A clinical photograph showing a skin lesion · the chart records prior malignancy (patient or family) · a female patient in their late 70s · the patient is Fitzpatrick phototype II — 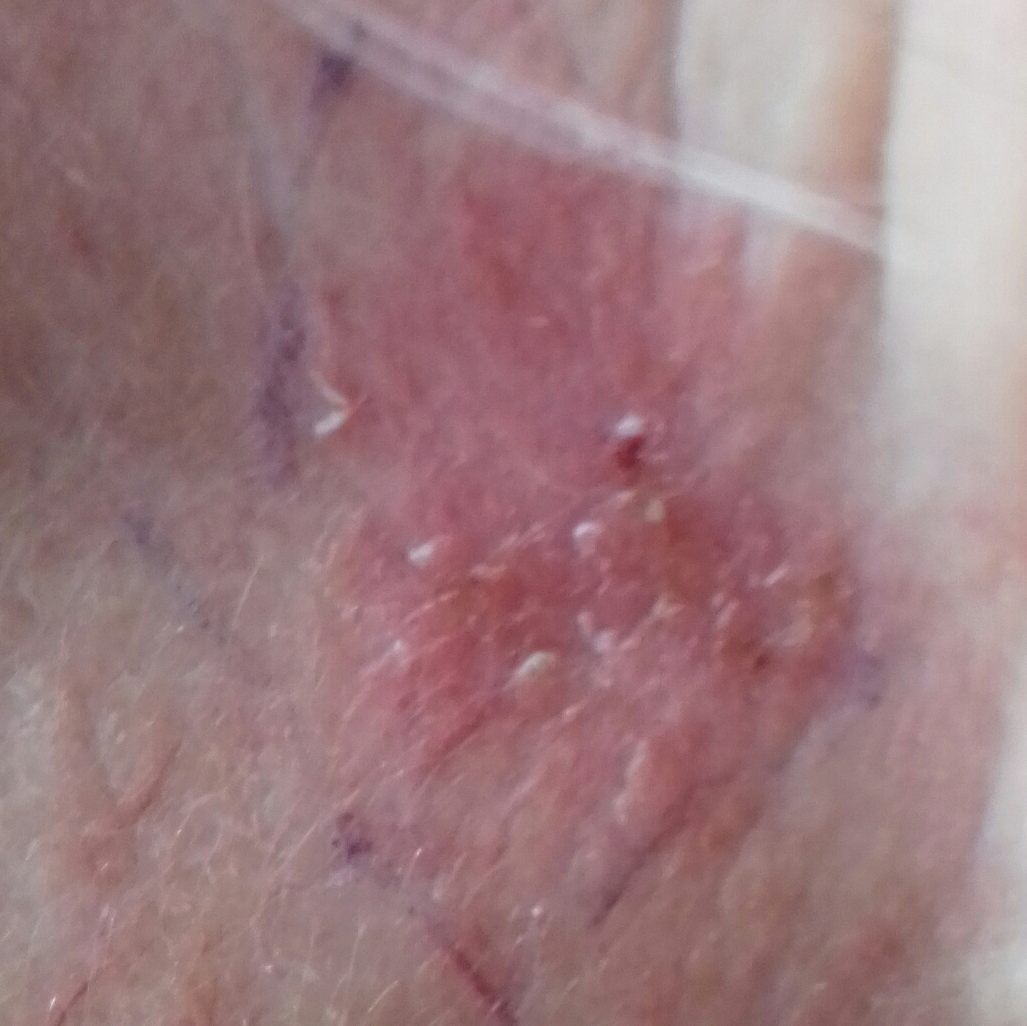| field | value |
|---|---|
| anatomic site | an ear |
| size | approx. 16 × 15 mm |
| patient-reported symptoms | growth, elevation / no change in appearance, no pain |
| pathology | squamous cell carcinoma (biopsy-proven) |